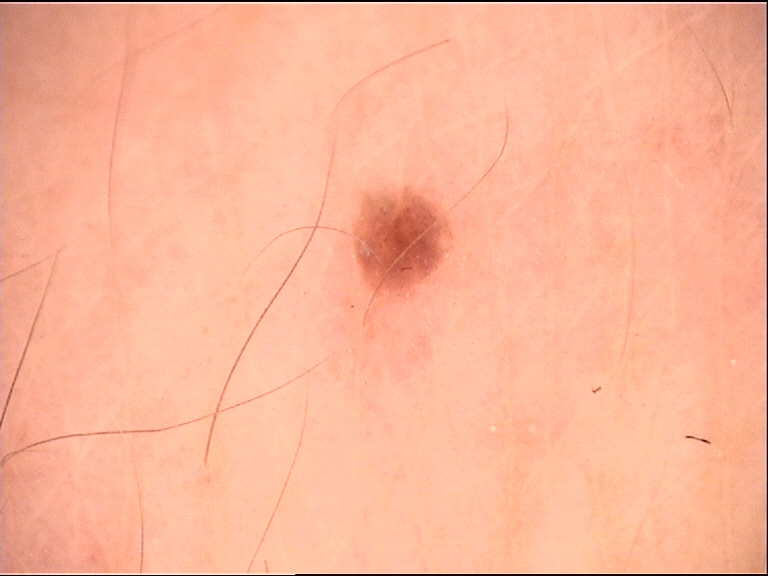Conclusion: Classified as a dysplastic junctional nevus.